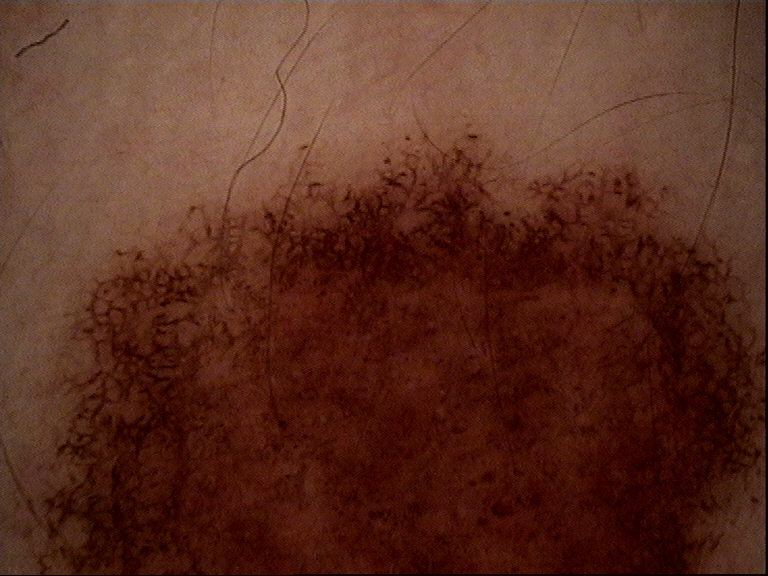Summary: A dermoscopic image of a skin lesion. Conclusion: The diagnostic label was a benign lesion — a congenital dysplastic compound nevus.